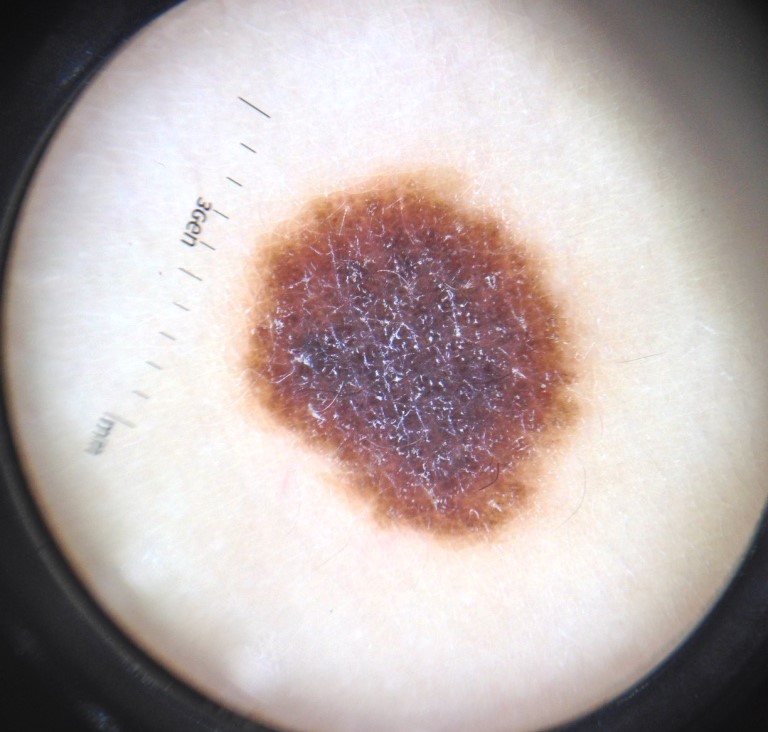Q: What kind of image is this?
A: dermatoscopy
Q: What is this lesion?
A: congenital compound nevus (expert consensus)